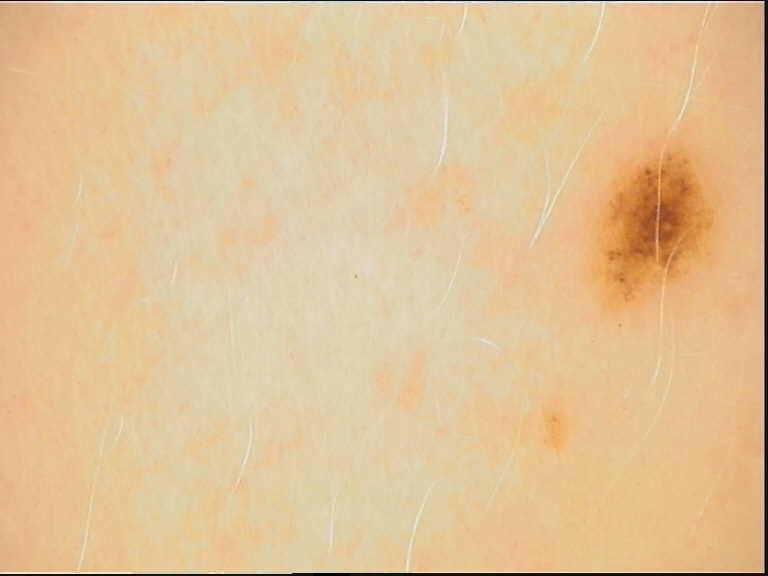{"image": "dermatoscopy", "diagnosis": {"name": "dysplastic junctional nevus", "code": "jd", "malignancy": "benign", "super_class": "melanocytic", "confirmation": "expert consensus"}}